This is a close-up image · the leg and arm are involved.
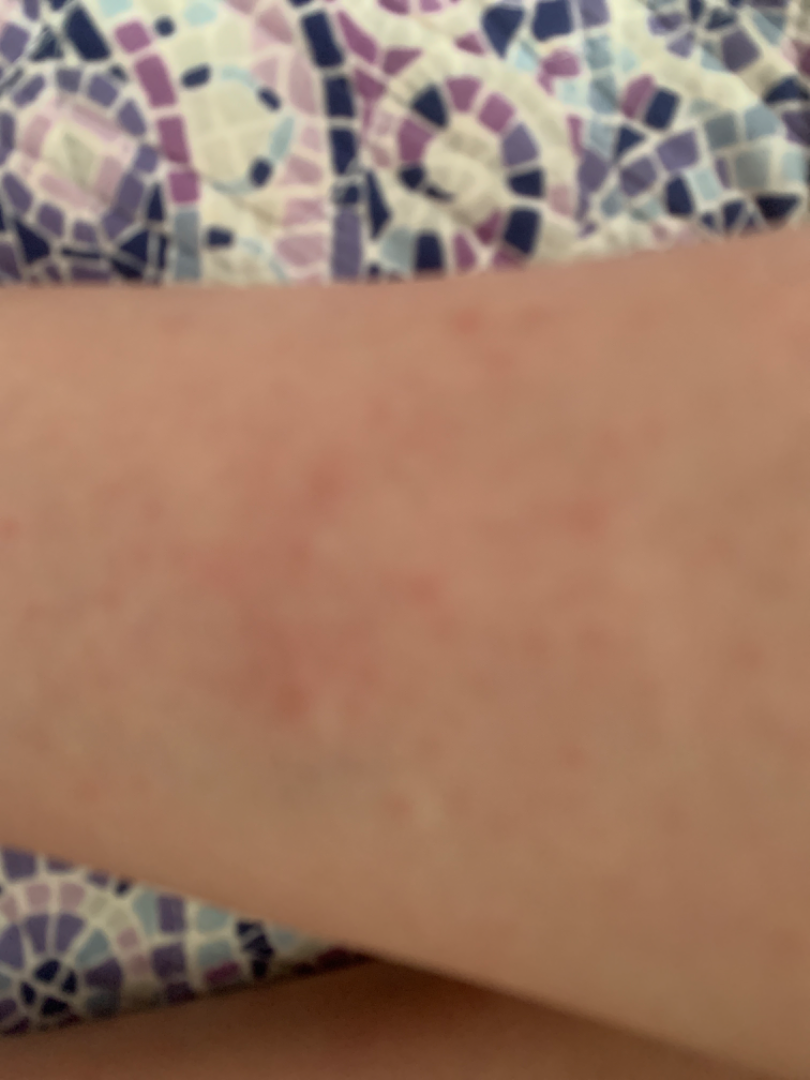{
  "assessment": "indeterminate"
}